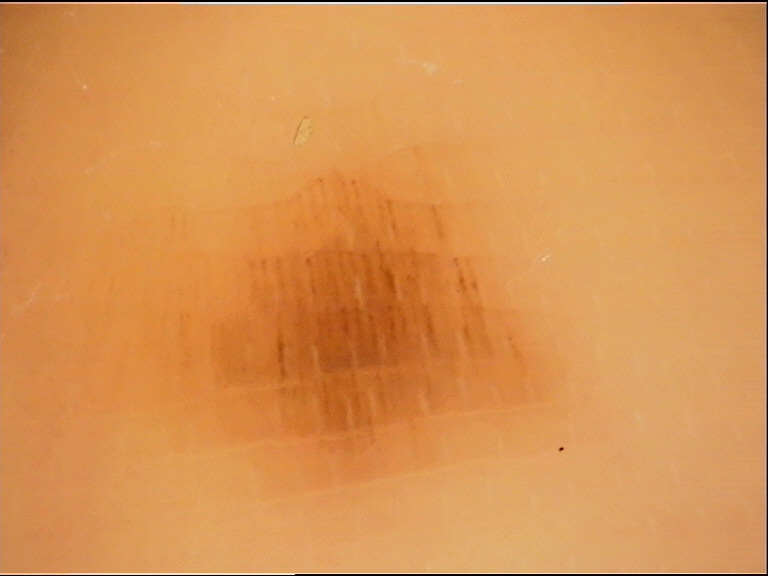Findings:
* label — acral junctional nevus (expert consensus)